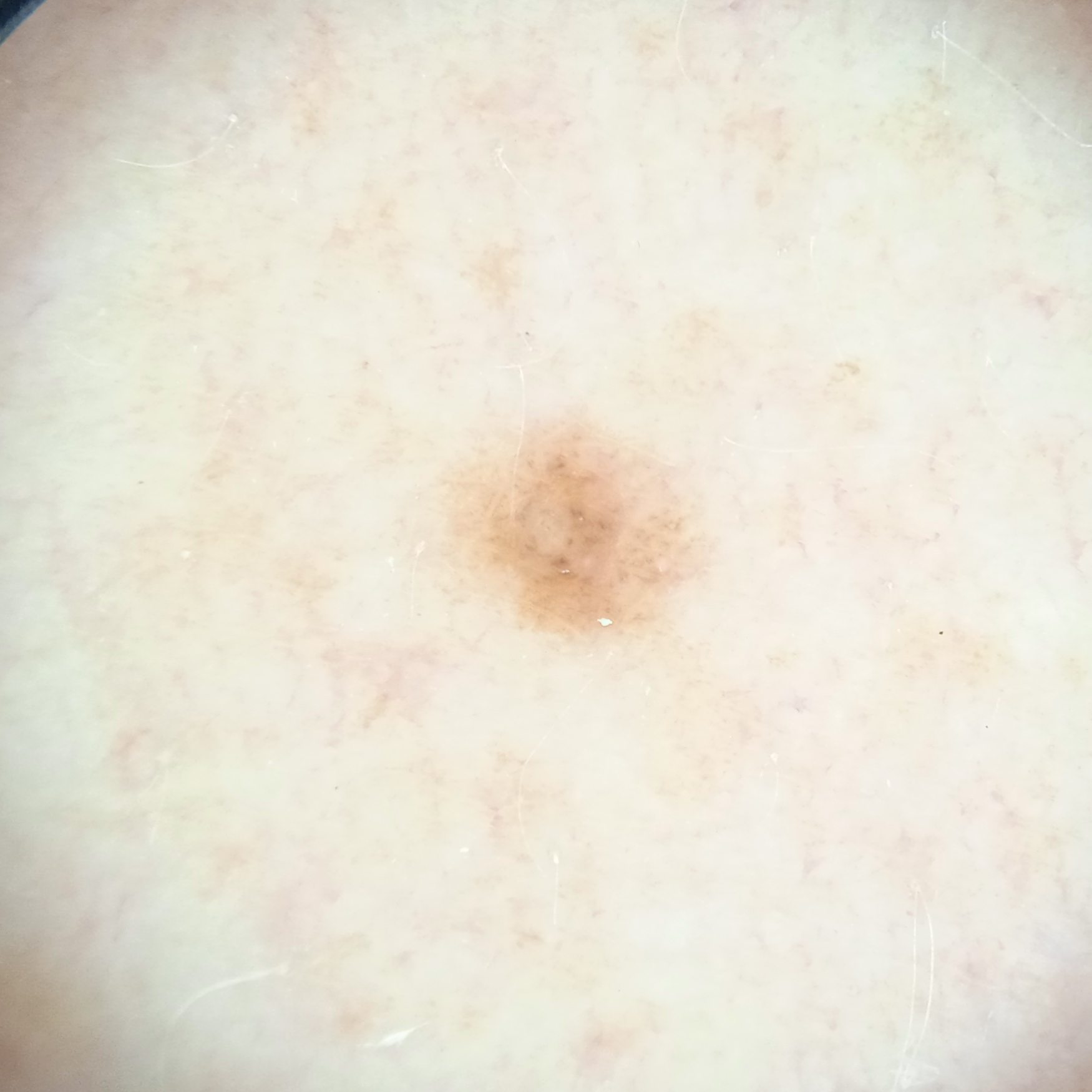Imaged for a research study, with no referral diagnosis recorded. A dermatoscopic image of a skin lesion. The lesion is on an arm. The lesion measures approximately 2.7 mm. The diagnostic impression was a melanocytic nevus.